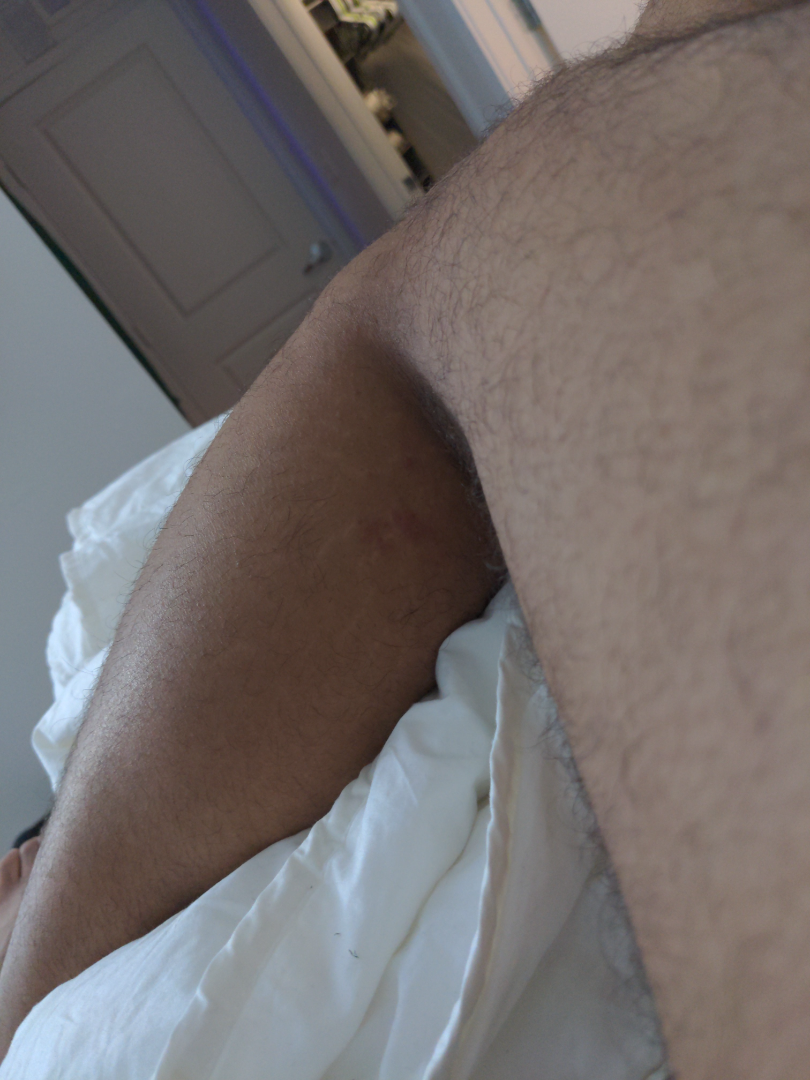The reviewer was unable to grade this case for skin condition.